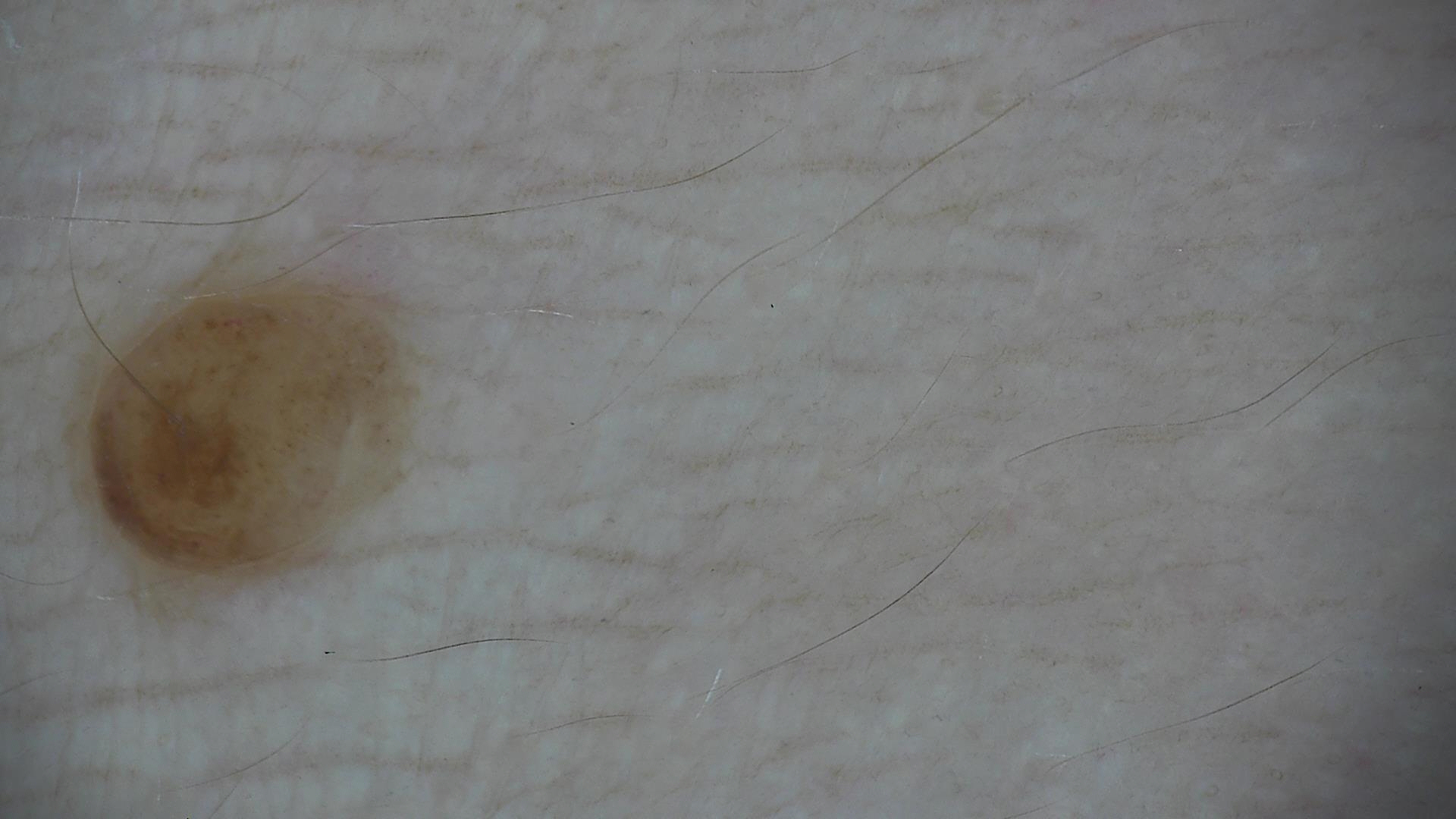Summary:
A dermoscopic photograph of a skin lesion. The morphology is that of a banal lesion.
Impression:
Classified as a dermal nevus.